A male patient aged 64 · a smartphone photograph of a skin lesion:
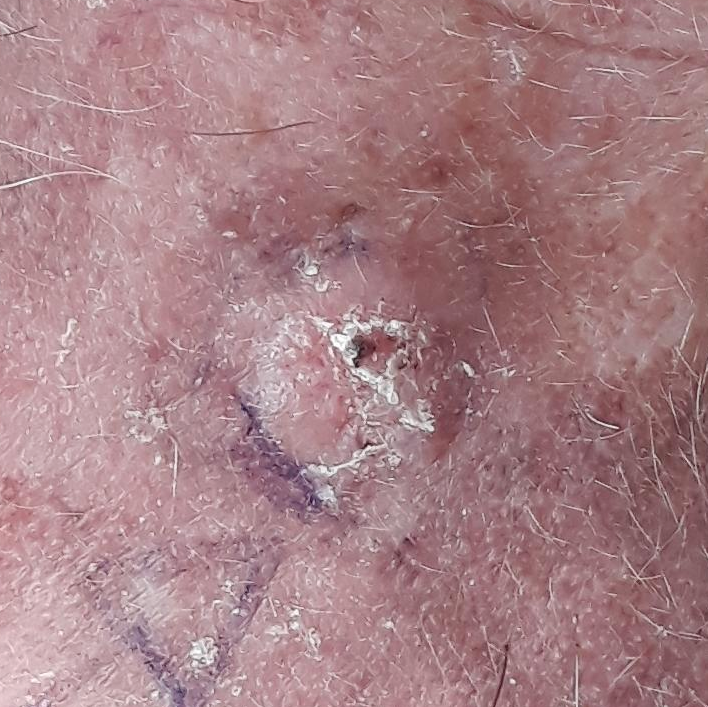The lesion involves the face. The patient describes that the lesion has grown, hurts, has bled, itches, and is elevated. Confirmed on histopathology as a squamous cell carcinoma.